A dermoscopic view of a skin lesion.
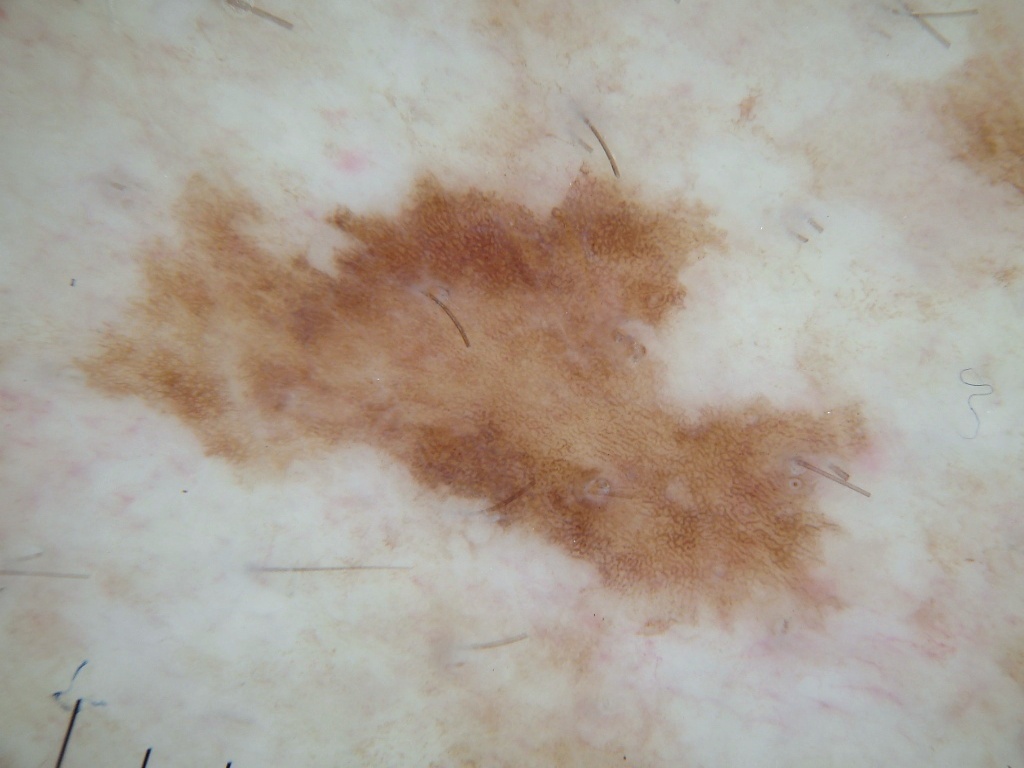Q: Where is the lesion located?
A: left=73, top=164, right=867, bottom=617
Q: What is the diagnosis?
A: a benign skin lesion